An image taken at an angle, the affected area is the leg — 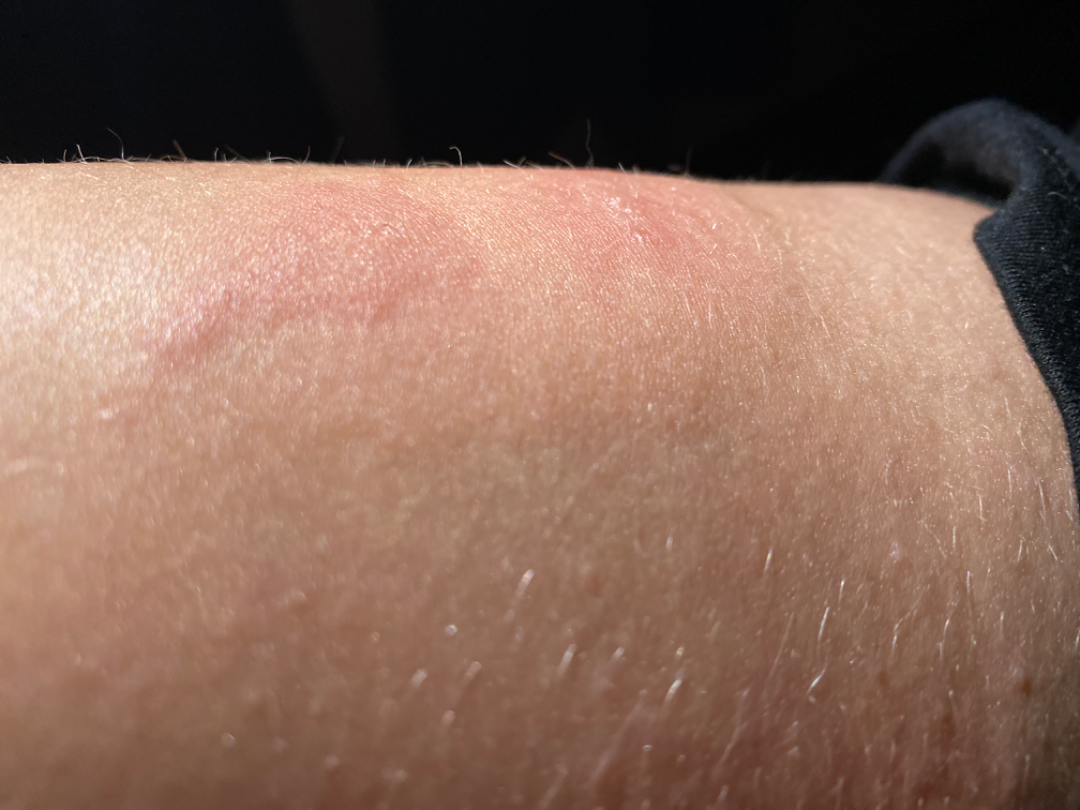Q: What was the assessment?
A: indeterminate